A close-up photograph, present for more than one year, the affected area is the leg: 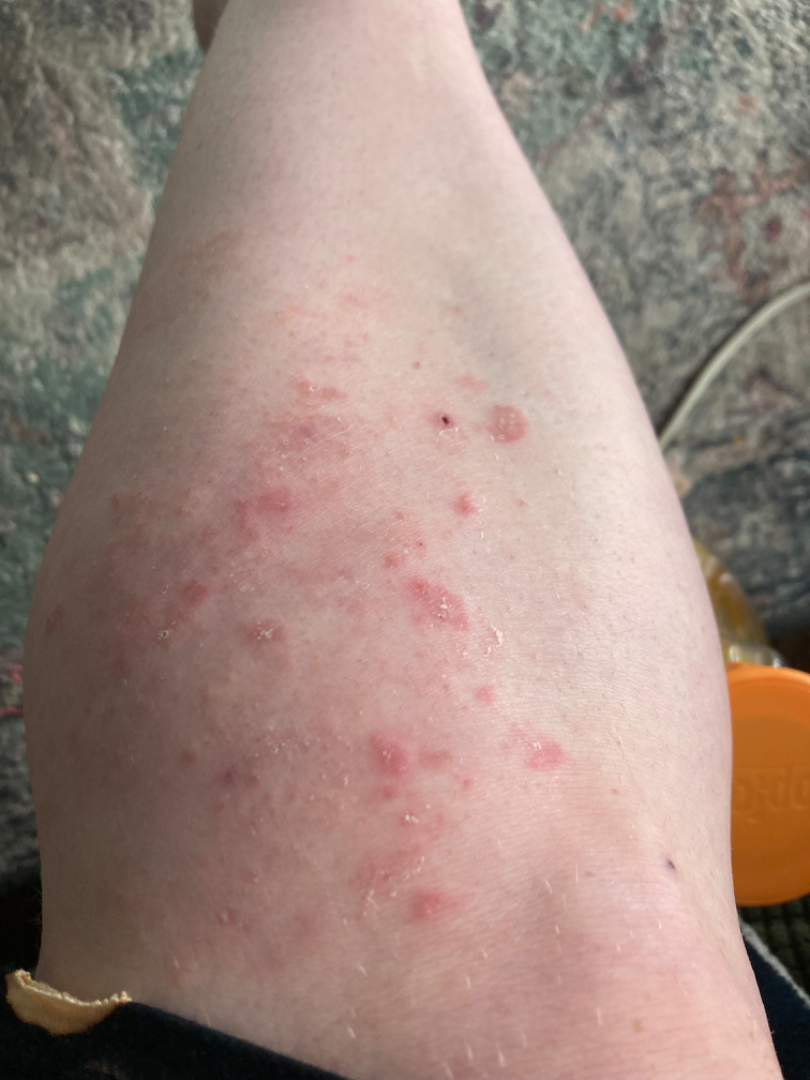differential: Tinea